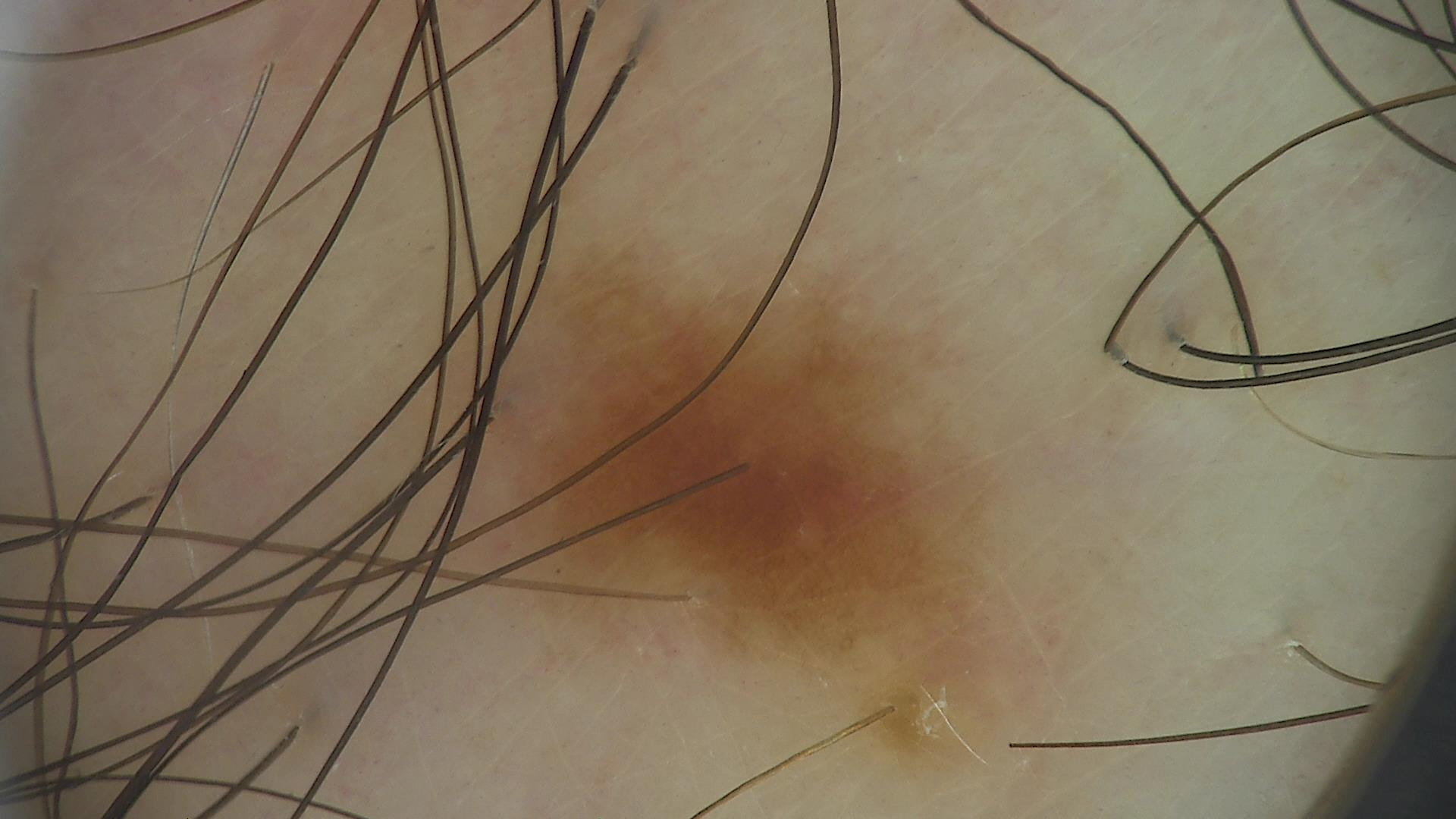- imaging — dermoscopy
- classification — banal
- label — junctional nevus (expert consensus)